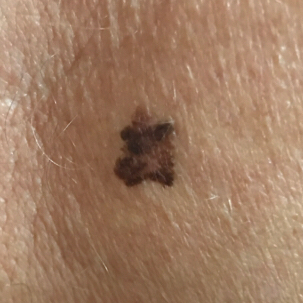exposures=prior skin cancer (patient or family), prior malignancy (patient or family), tobacco use, no pesticide exposure, no alcohol use
image=clinical photograph
Fitzpatrick=II
location=the back
diameter=approx. 10 × 10 mm
patient-reported symptoms=growth, change in appearance, elevation
pathology=melanoma (biopsy-proven)